A dermoscopic photograph of a skin lesion.
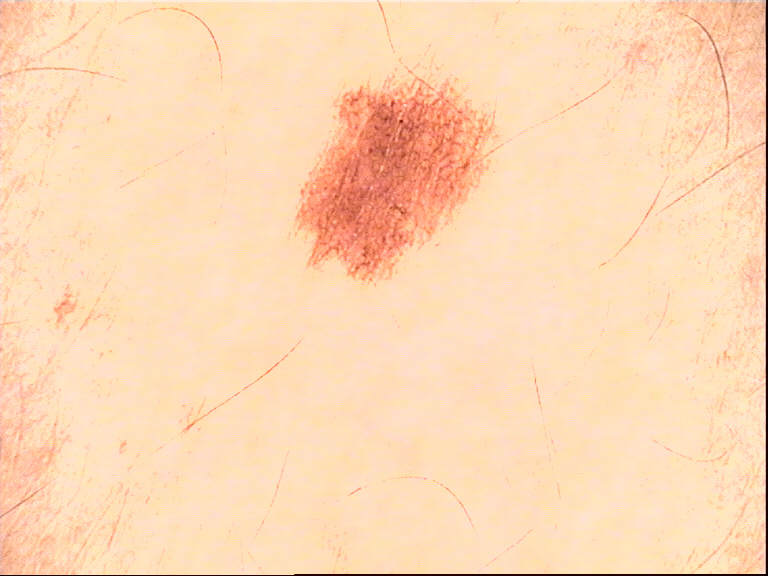Impression: The diagnosis was a dysplastic junctional nevus.